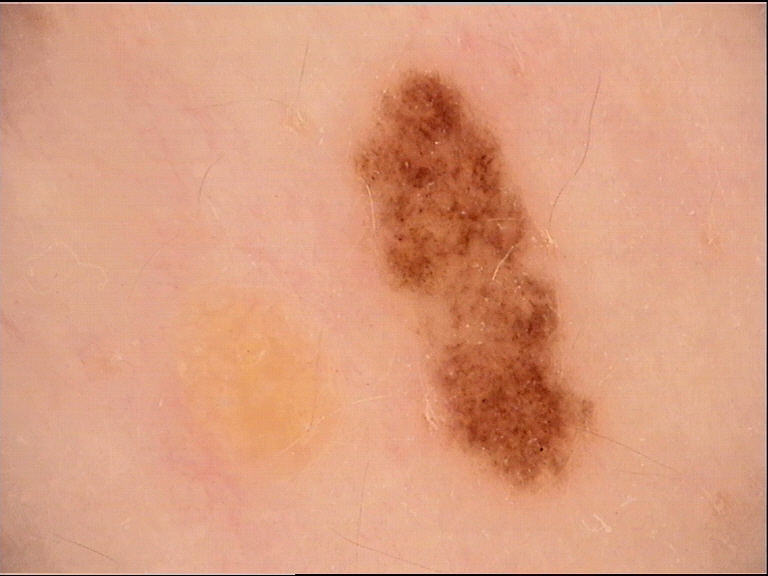Impression:
Consistent with a dysplastic junctional nevus.